The affected area is the leg, the patient is a male aged 30–39, the photograph was taken at an angle — 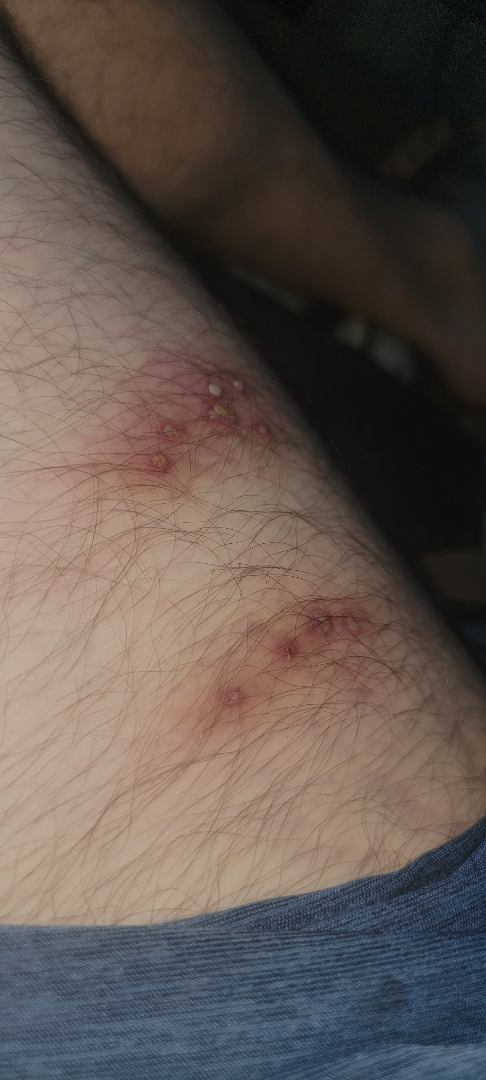clinical impression: Herpes Zoster (weight 0.41); Herpes Simplex (weight 0.41); Impetigo (weight 0.18).